A clinical photograph showing a skin lesion; acquired for a research image collection, with no referral diagnosis — 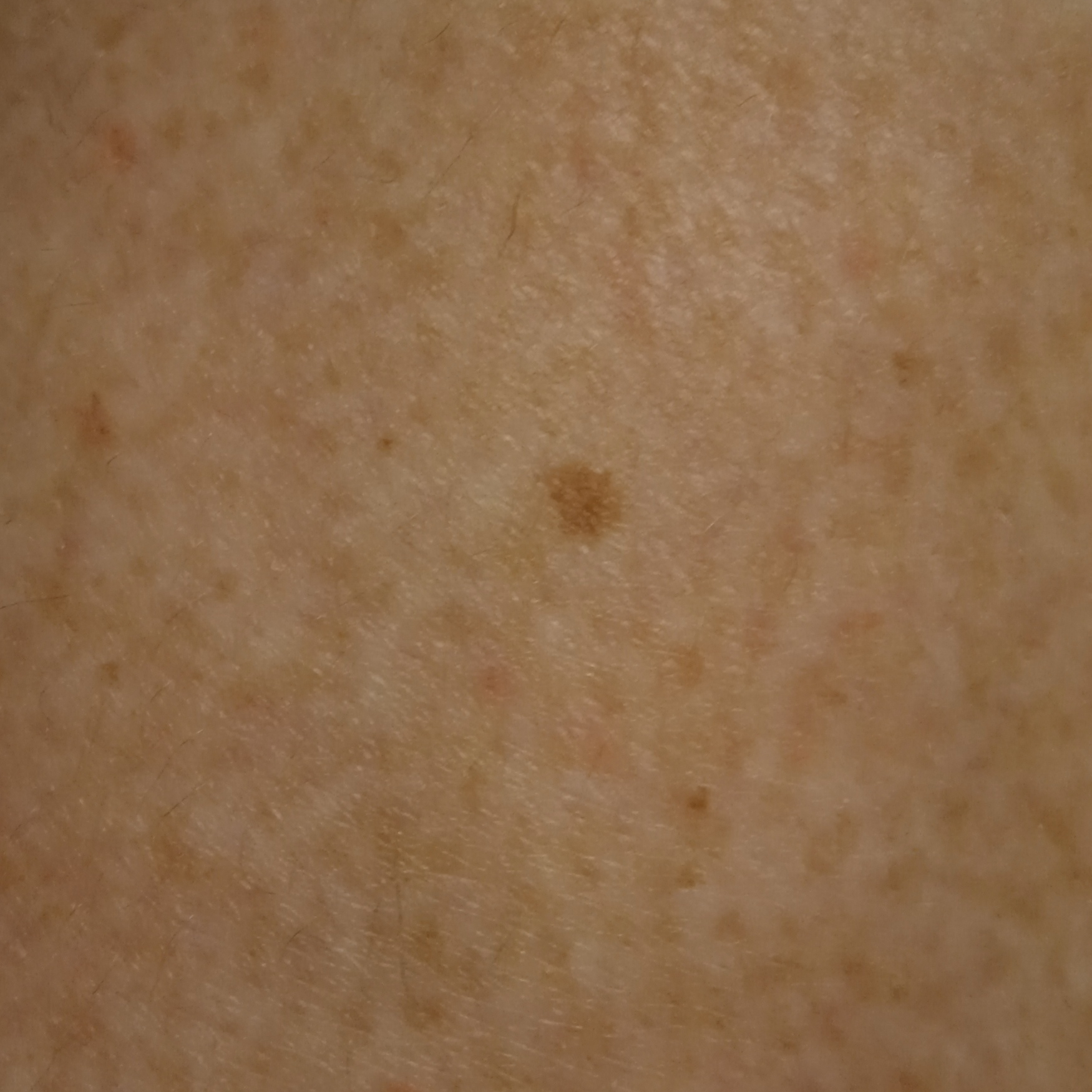The lesion is on a leg. Measuring roughly 4.1 mm. Dermatologist review favored a melanocytic nevus.